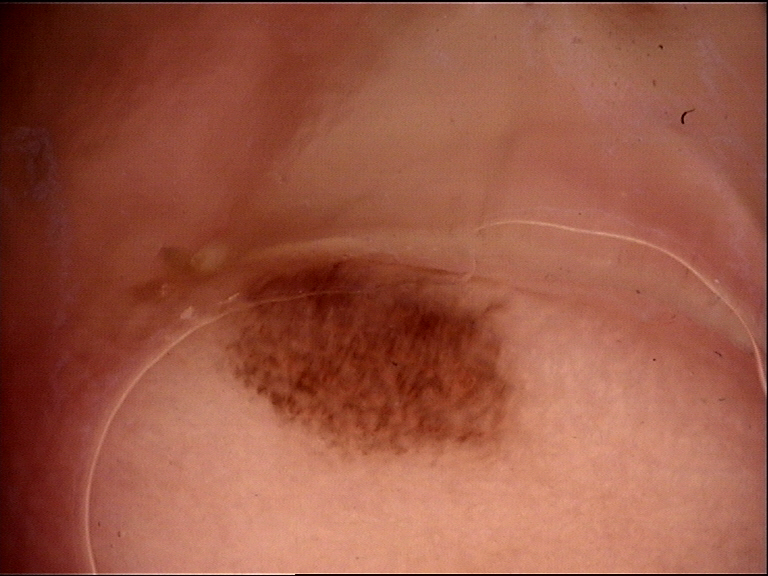{
  "image": "dermoscopy",
  "diagnosis": {
    "name": "acral junctional nevus",
    "code": "ajb",
    "malignancy": "benign",
    "super_class": "melanocytic",
    "confirmation": "expert consensus"
  }
}